A dermatoscopic image of a skin lesion: 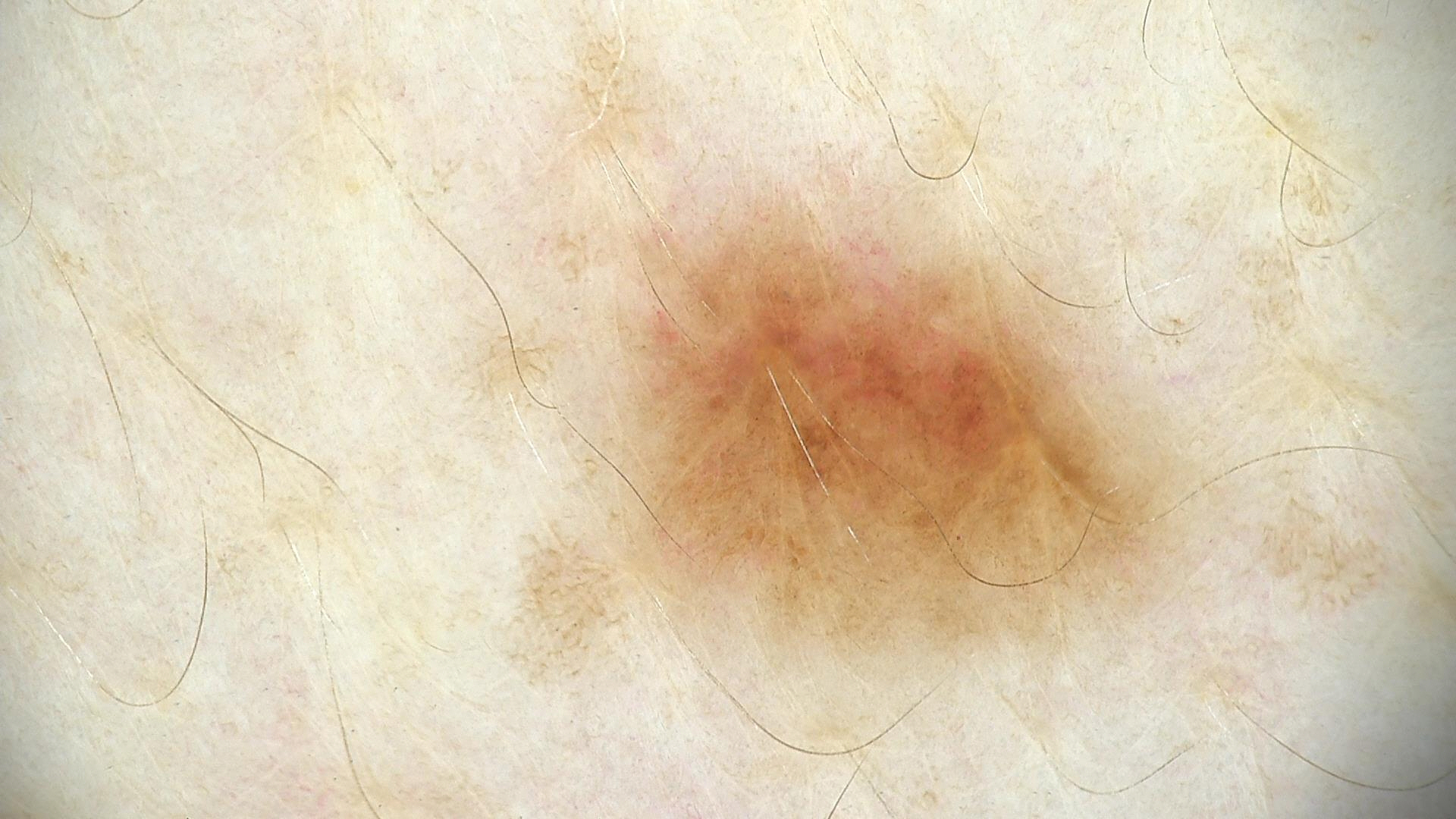Case:
– label: dysplastic junctional nevus (expert consensus)